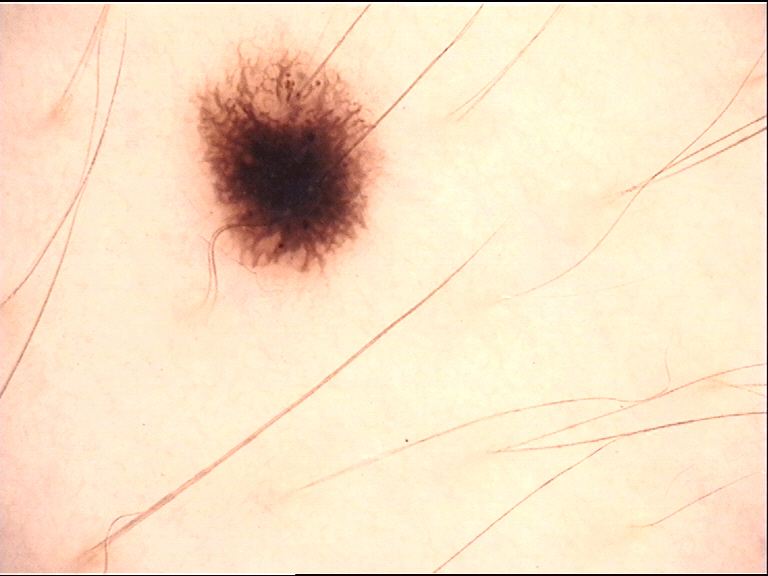Conclusion: Classified as a dysplastic junctional nevus.